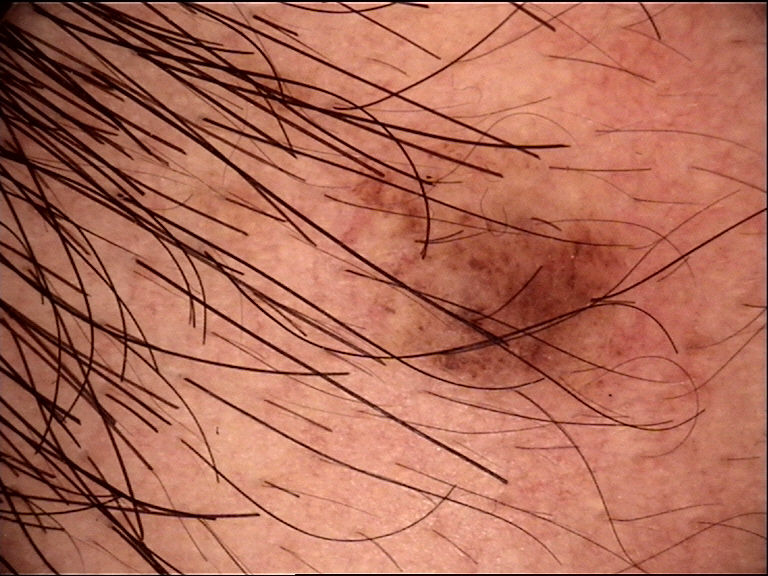Impression:
Classified as a compound nevus.